A smartphone photograph of a skin lesion:
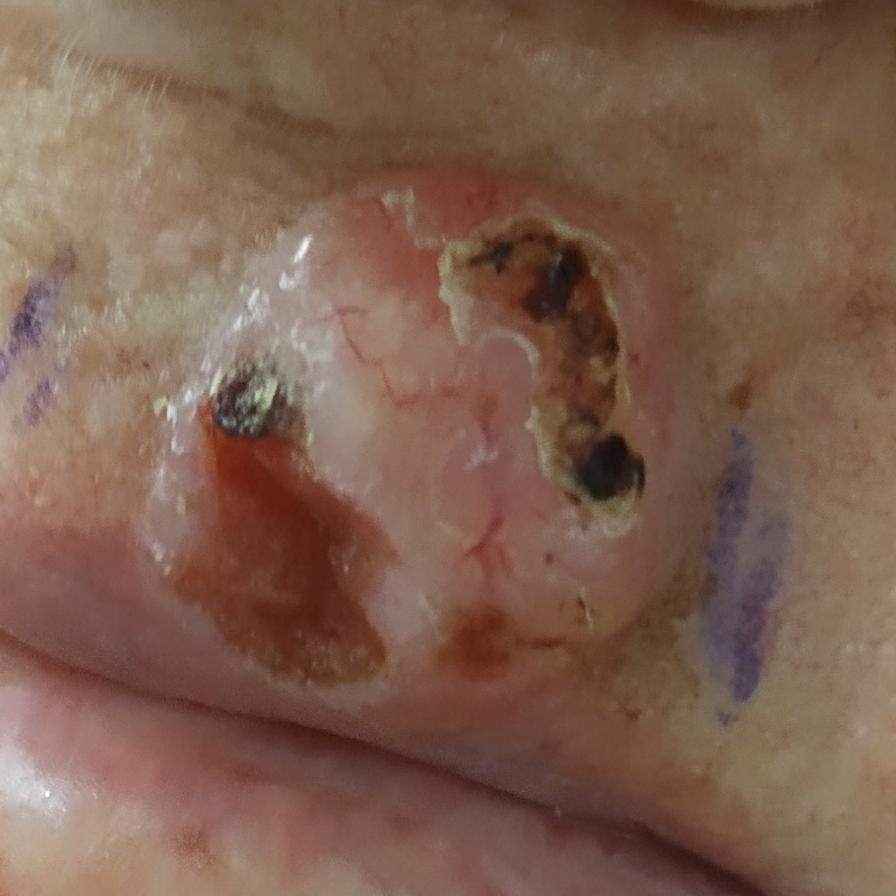Case summary: By the patient's account, the lesion itches, has bled, is elevated, and hurts, but has not changed and has not grown. Conclusion: Histopathology confirmed a basal cell carcinoma.